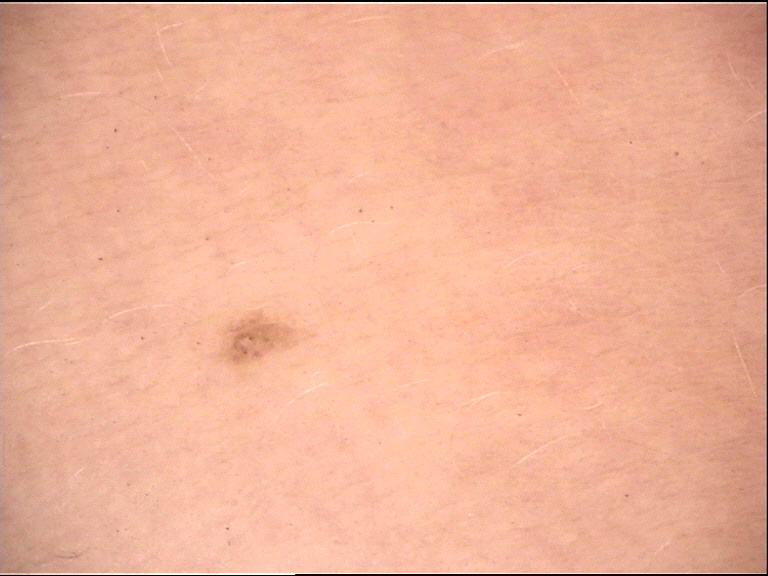Case:
• class · dysplastic junctional nevus (expert consensus)